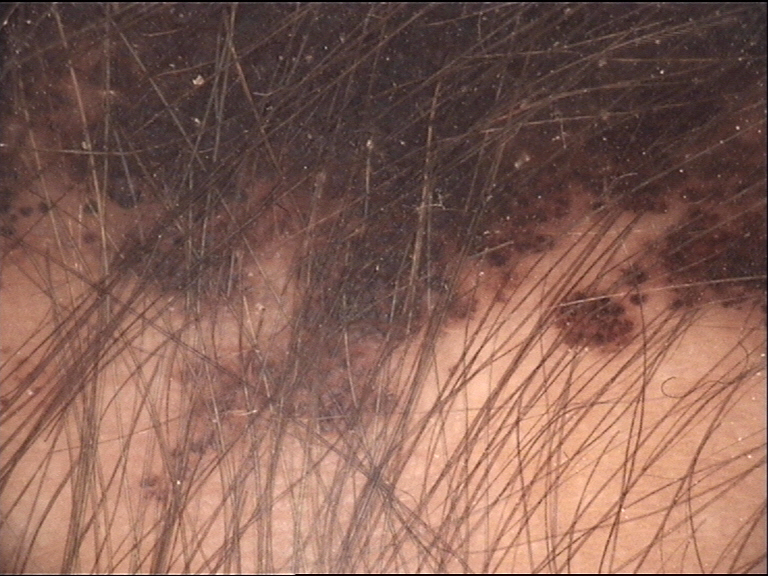Impression:
Diagnosed as a banal lesion — a congenital compound nevus.